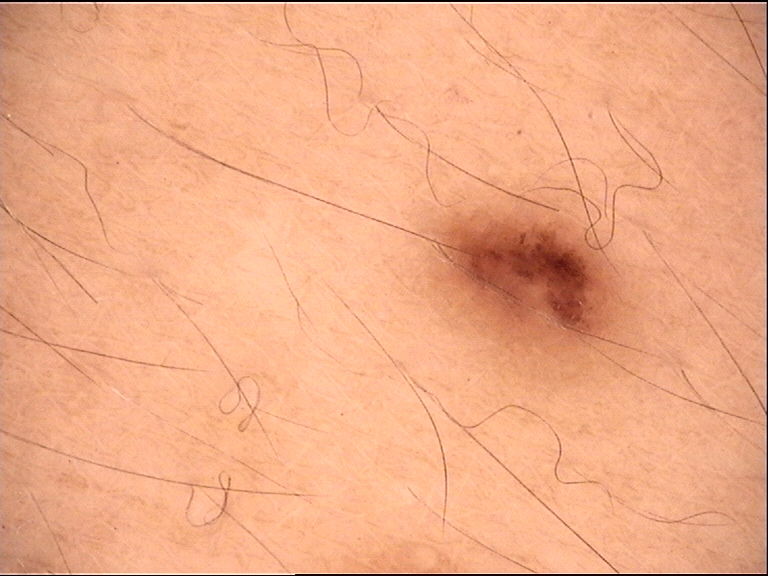{
  "diagnosis": {
    "name": "dysplastic junctional nevus",
    "code": "jd",
    "malignancy": "benign",
    "super_class": "melanocytic",
    "confirmation": "expert consensus"
  }
}